This image was taken at an angle.
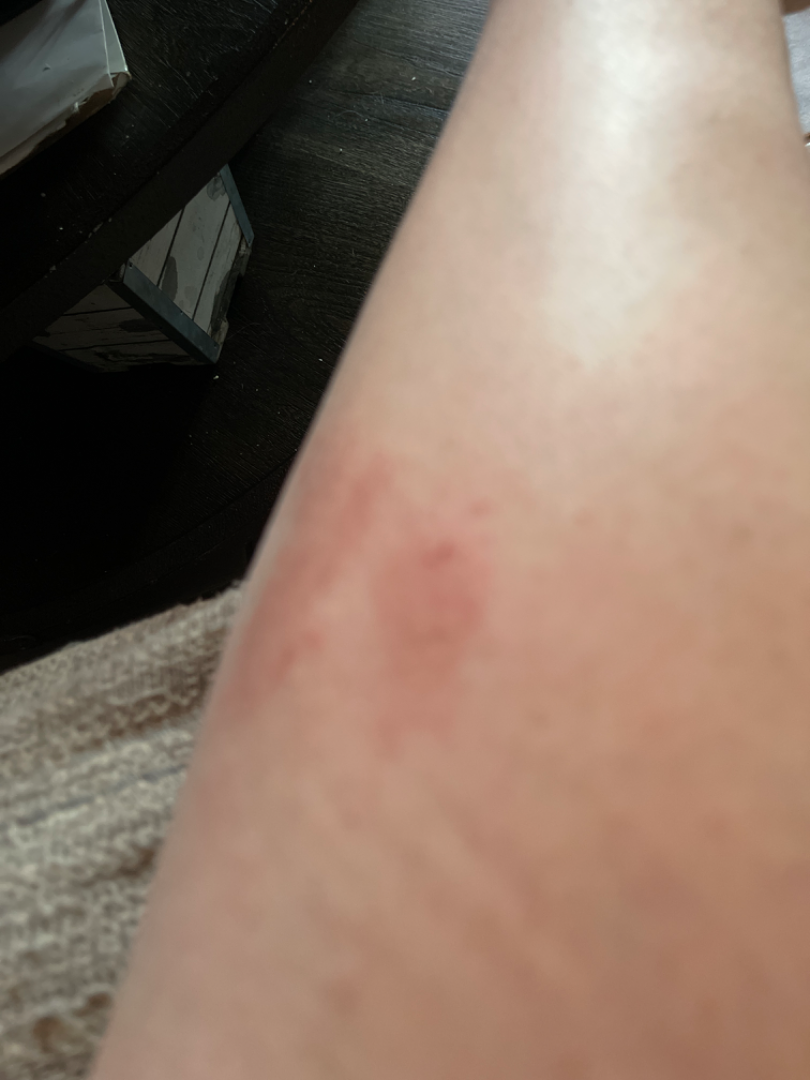– assessment · indeterminate from the photograph